The patient was assessed as skin type II. Per the chart, a previous melanoma but no melanoma in first-degree relatives. A female patient approximately 50 years of age.
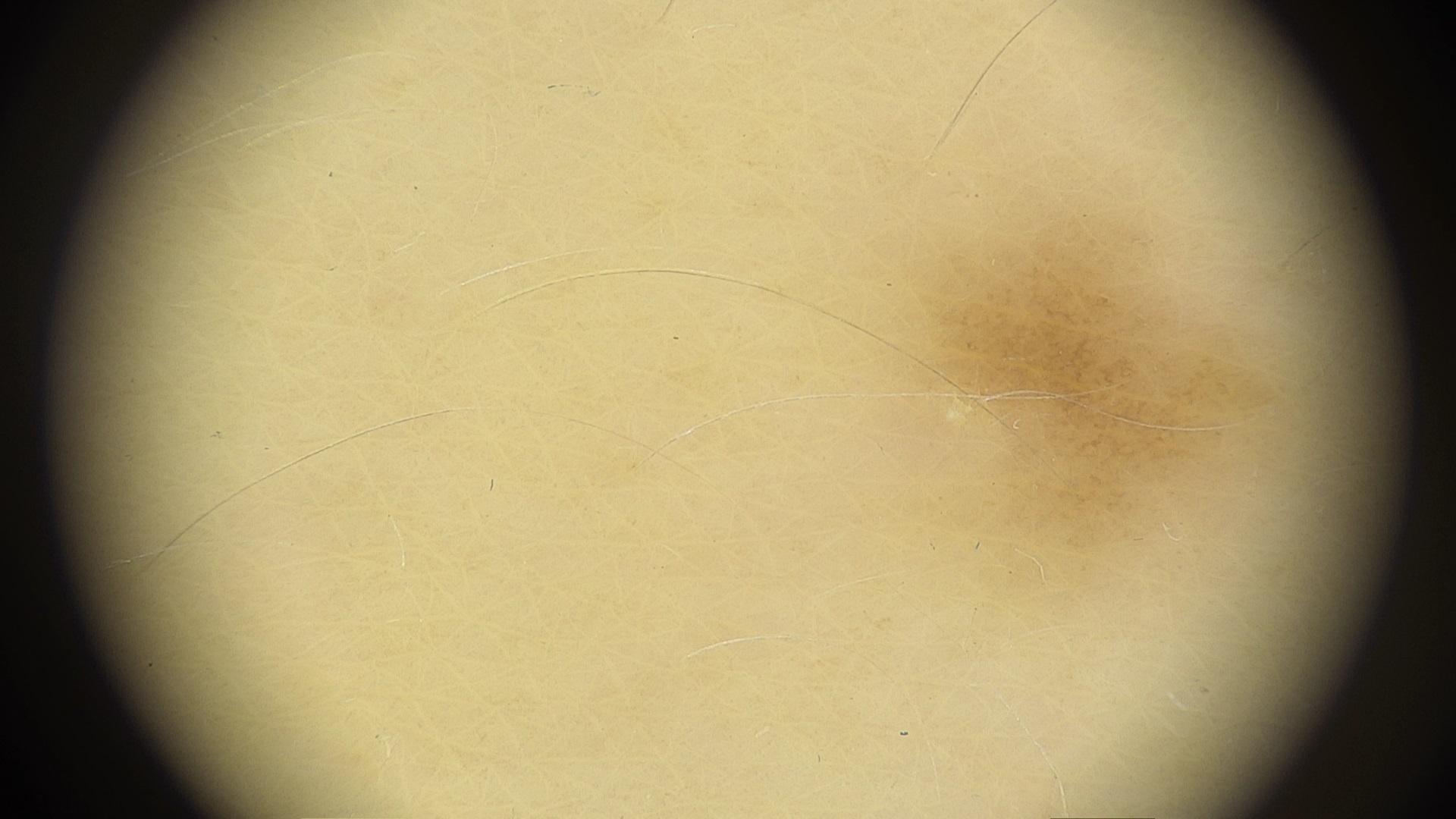Q: What is this lesion?
A: Solar lentigo (clinical impression)